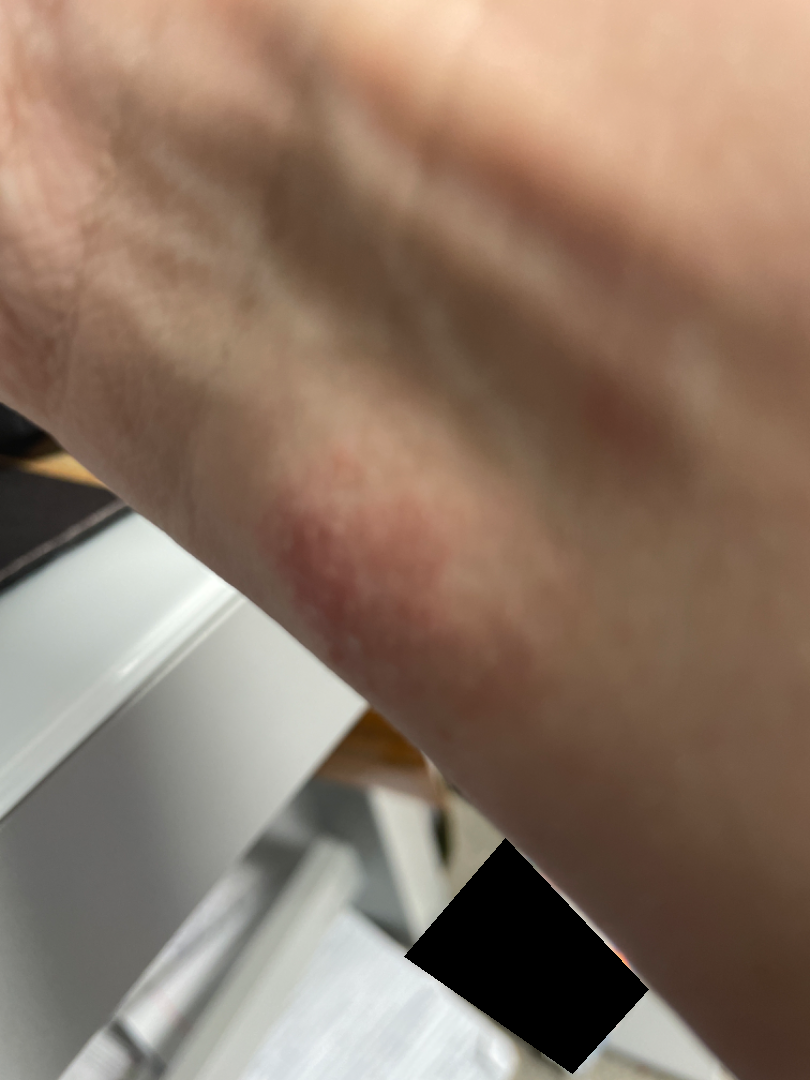Impression:
The image was not sufficient for the reviewer to characterize the skin condition.